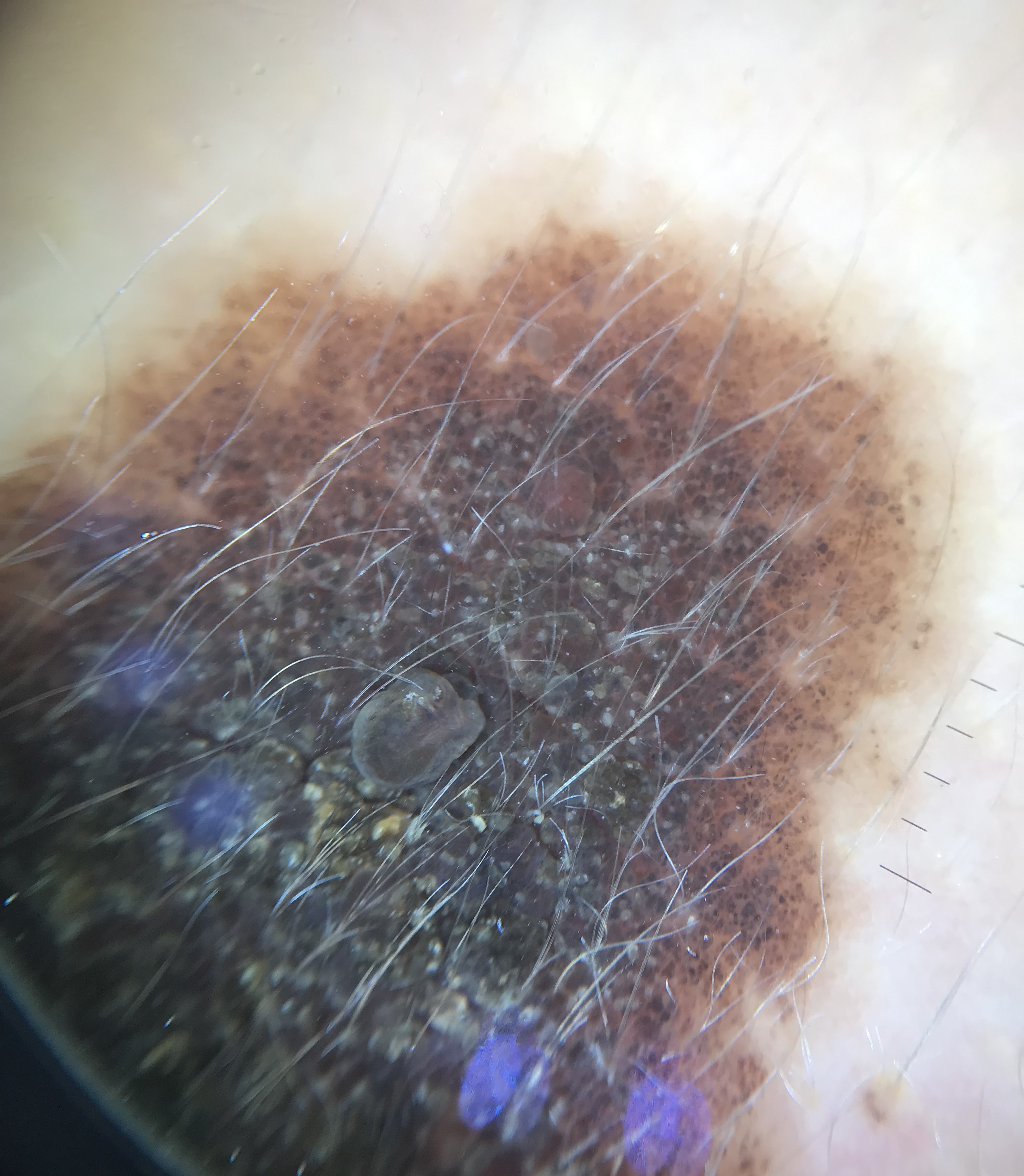| feature | finding |
|---|---|
| image type | dermoscopy |
| subtype | banal |
| class | congenital compound nevus (expert consensus) |